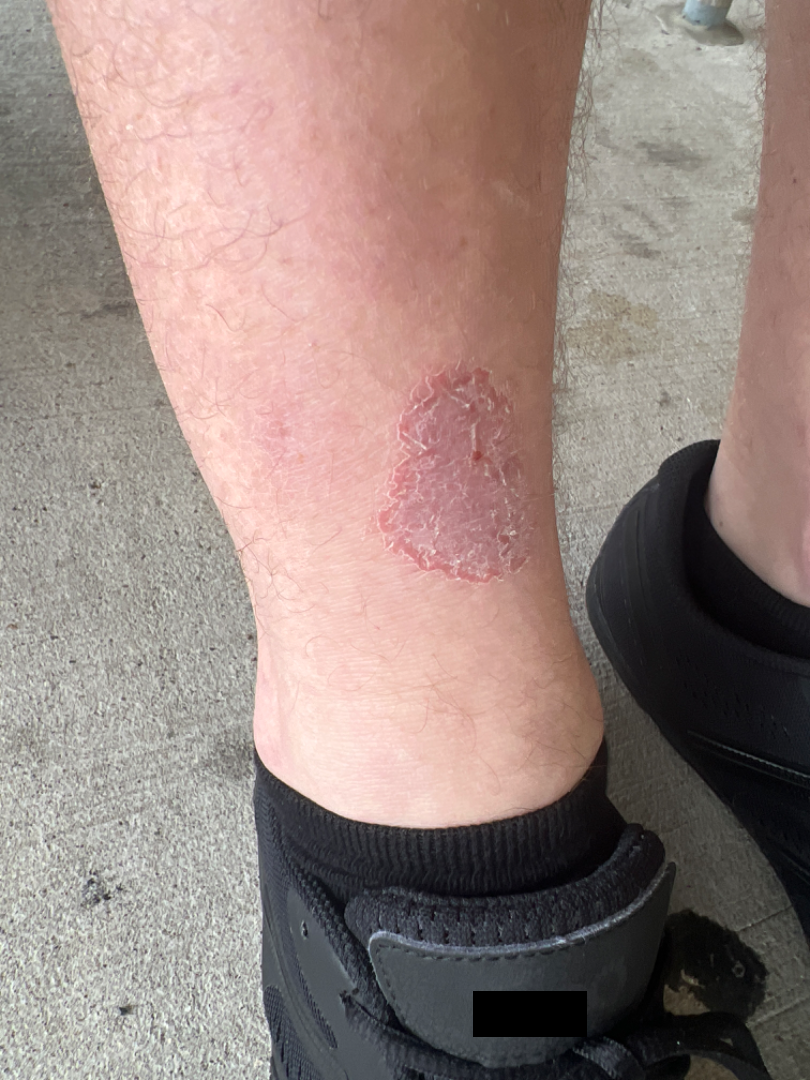Patient information:
The photo was captured at an angle.
Review:
One reviewing dermatologist: Eczema and Acute and chronic dermatitis were considered with similar weight.